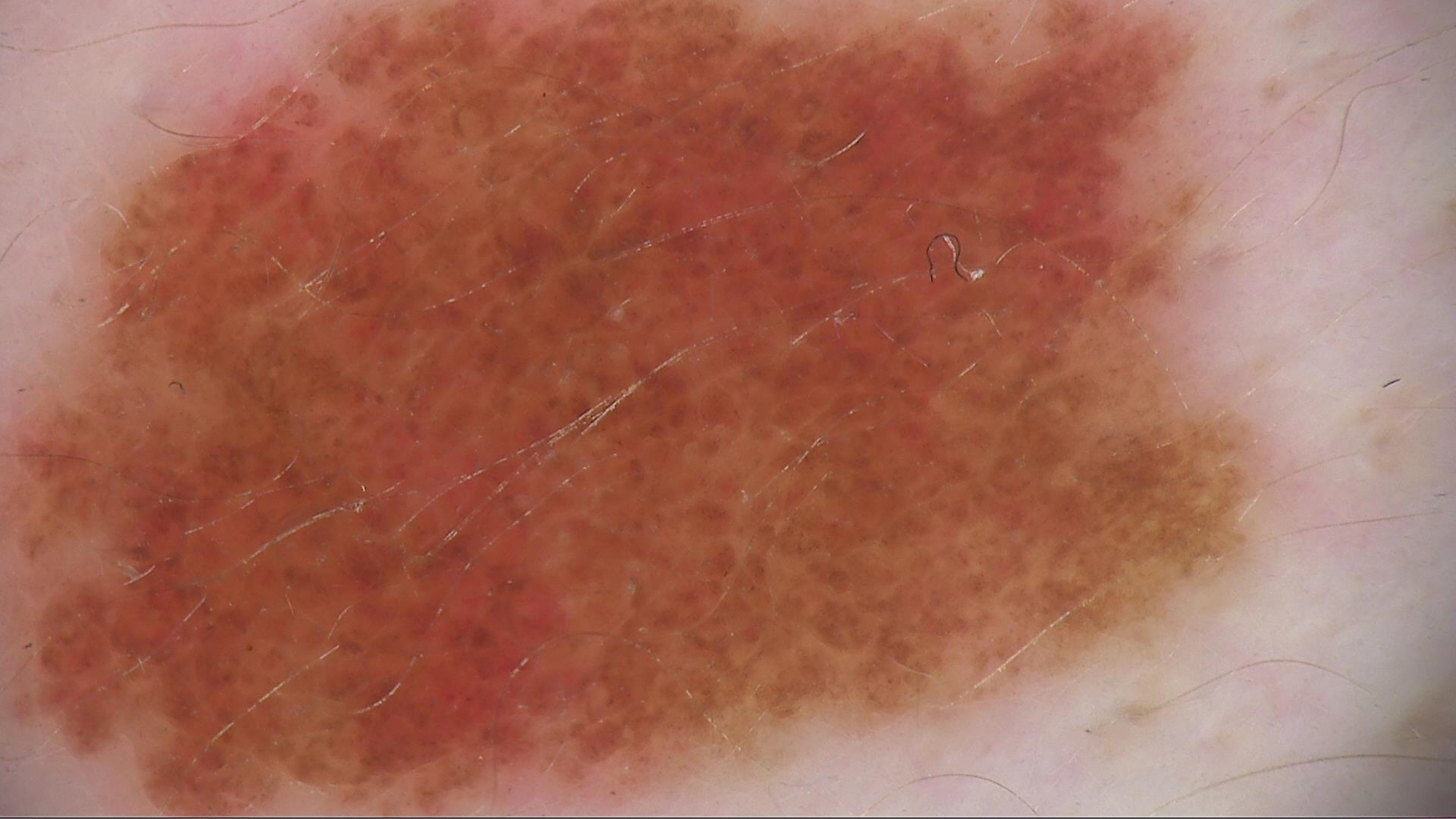The morphology is that of a banal lesion.
Labeled as a compound nevus.